The affected area is the leg and arm; female subject, age 40–49; no associated systemic symptoms reported; the patient indicates itching, bothersome appearance, enlargement and burning; self-categorized by the patient as a rash; this image was taken at an angle; the patient indicates the condition has been present for less than one week; the patient indicates the lesion is raised or bumpy: 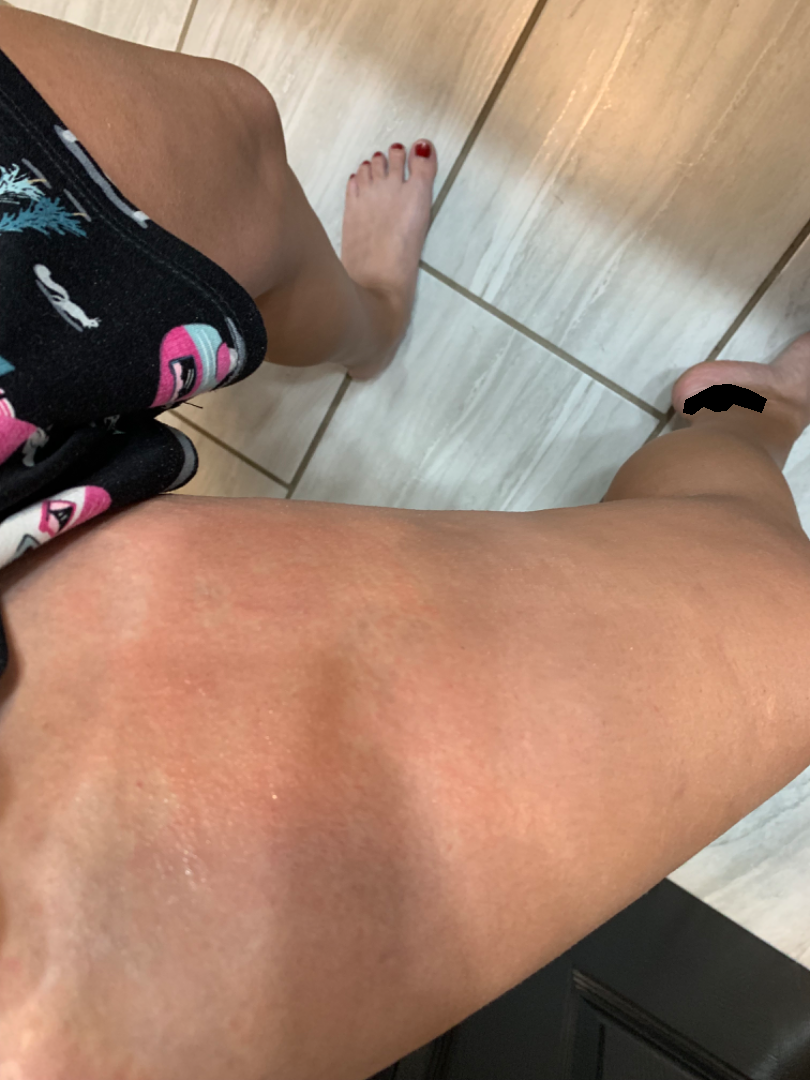Findings:
The reviewing dermatologist's impression was: Urticaria (100%).